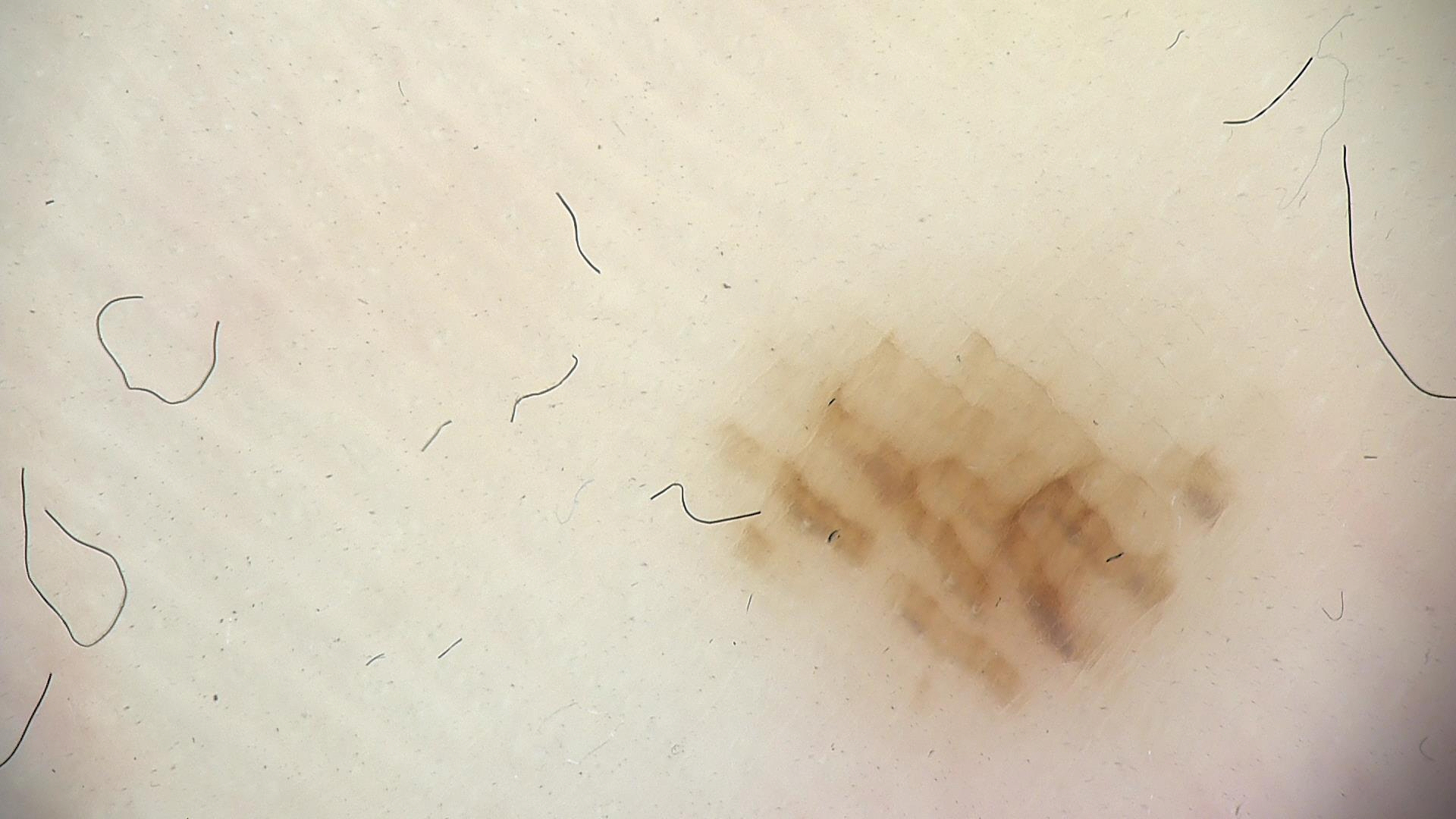| key | value |
|---|---|
| image | dermoscopy |
| label | acral dysplastic junctional nevus (expert consensus) |